Skin tone: FST IV; lay graders estimated MST 3 or 4, this is a close-up image: 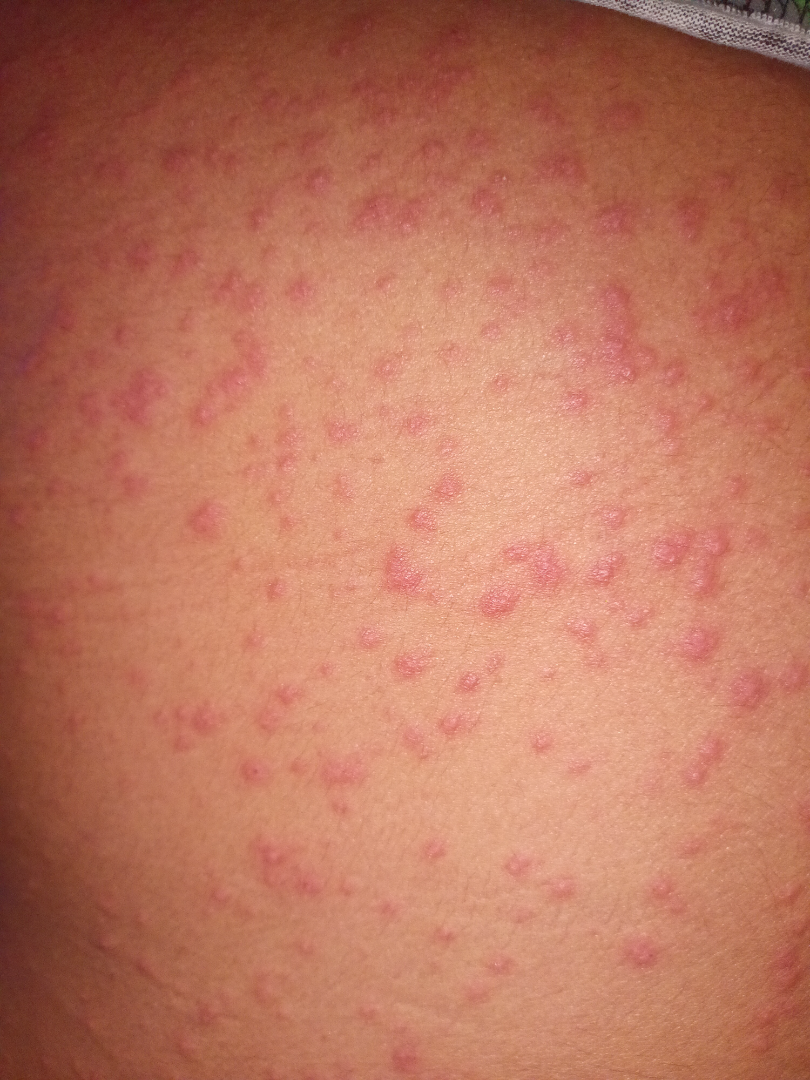<dermatology_case>
  <differential>
    <tied_lead>Lichen planus/lichenoid eruption, Psoriasis, Eczema</tied_lead>
  </differential>
</dermatology_case>